A subject 56 years of age · a clinical close-up photograph of a skin lesion: 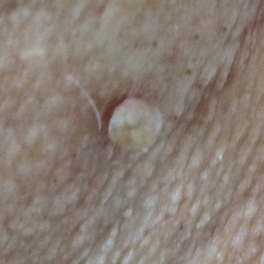{
  "lesion_location": "an arm",
  "symptoms": {
    "present": [
      "bleeding",
      "elevation"
    ],
    "absent": [
      "change in appearance",
      "growth"
    ]
  },
  "diagnosis": {
    "name": "seborrheic keratosis",
    "code": "SEK",
    "malignancy": "benign",
    "confirmation": "clinical consensus"
  }
}